A dermoscopy image of a single skin lesion: 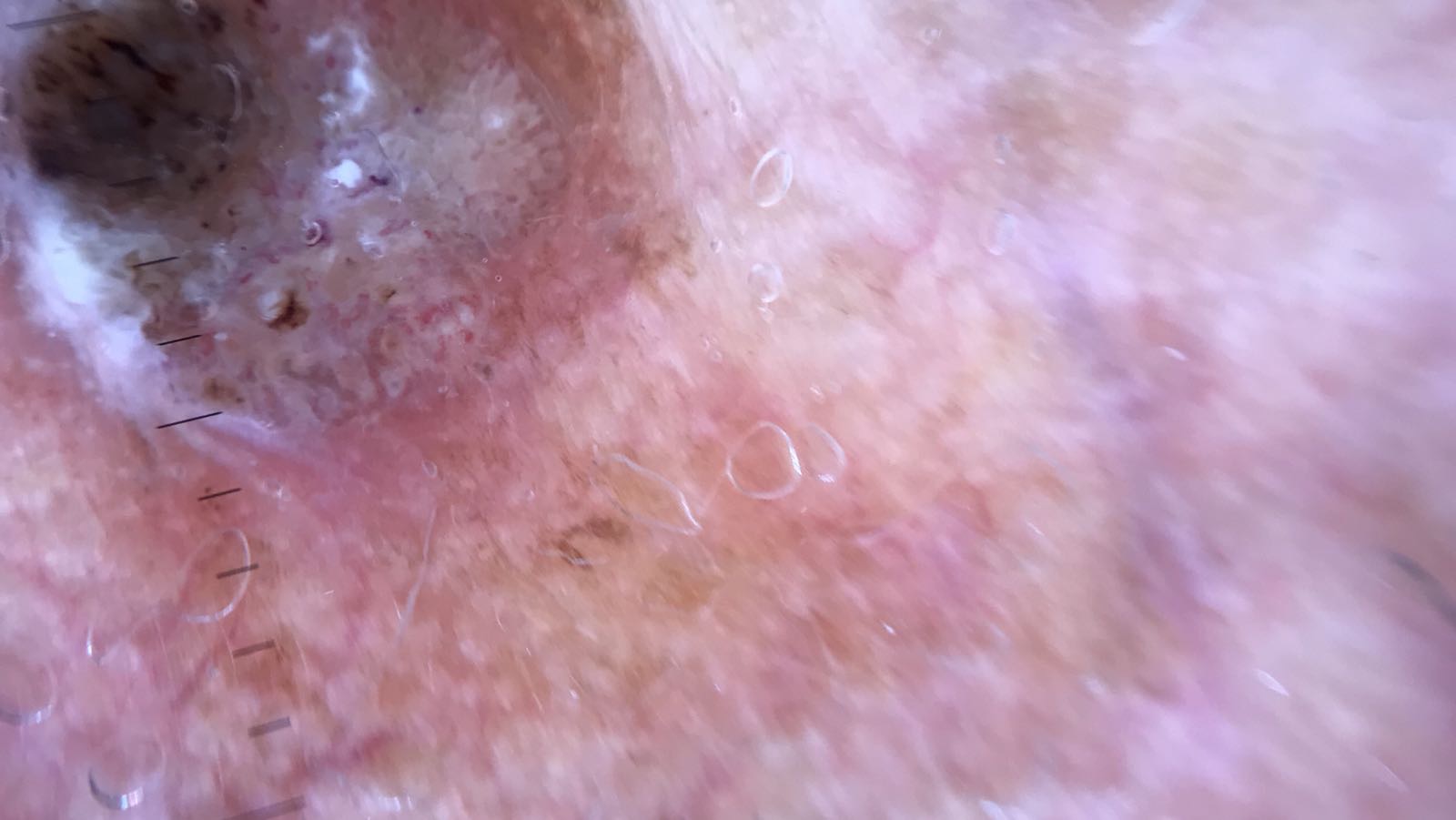<dermoscopy>
  <lesion_type>
    <main_class>keratinocytic</main_class>
  </lesion_type>
  <diagnosis>
    <name>seborrheic keratosis</name>
    <code>sk</code>
    <malignancy>benign</malignancy>
    <super_class>non-melanocytic</super_class>
    <confirmation>expert consensus</confirmation>
  </diagnosis>
</dermoscopy>